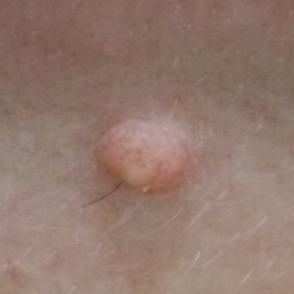A clinical photograph of a skin lesion.
A subject in their mid-40s.
The lesion was found on the face.
The consensus clinical diagnosis was a nevus.